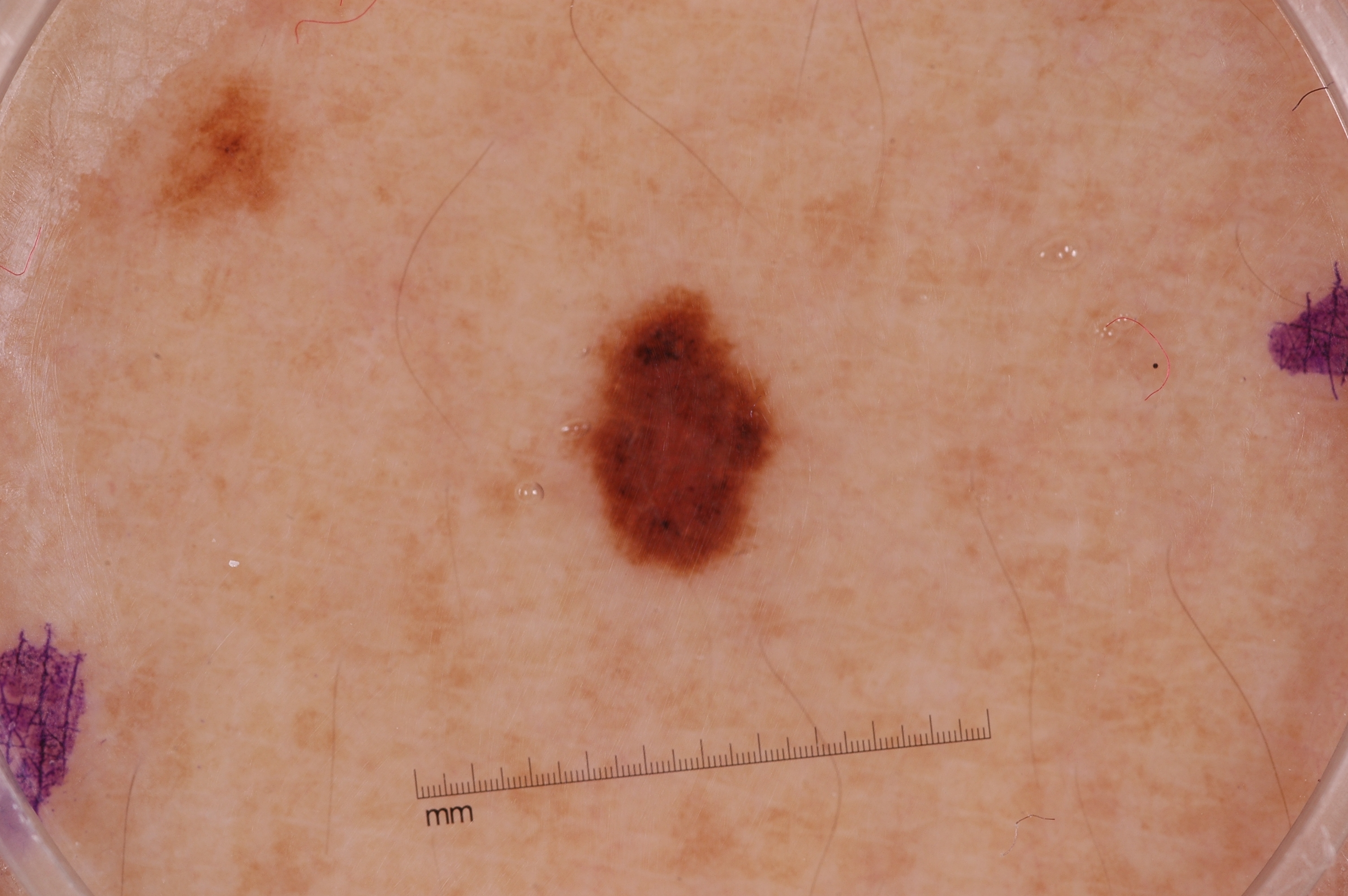Case summary:
- image type · dermoscopic image
- patient · female, in their mid- to late 40s
- dermoscopic features assessed but absent · pigment network, negative network, streaks, and milia-like cysts
- bounding box · [579, 294, 790, 574]
- size · small
- impression · a melanocytic nevus